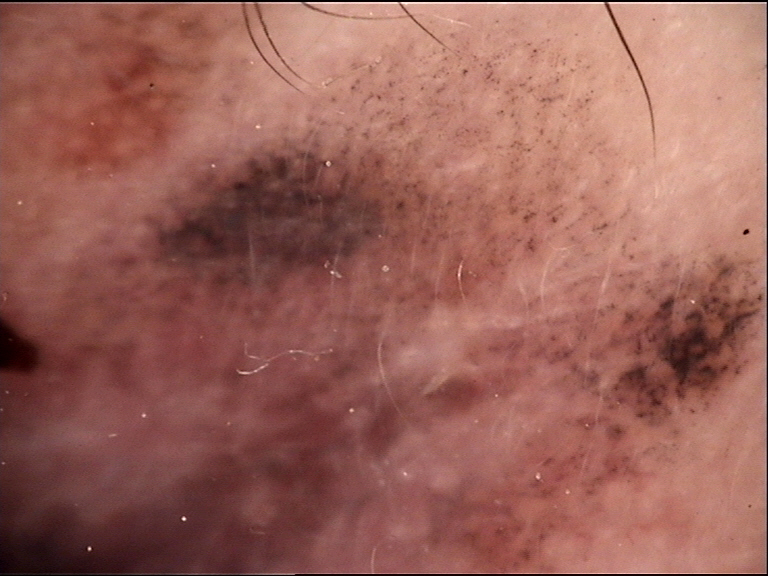| field | value |
|---|---|
| imaging | dermatoscopy |
| class | lentigo maligna (biopsy-proven) |